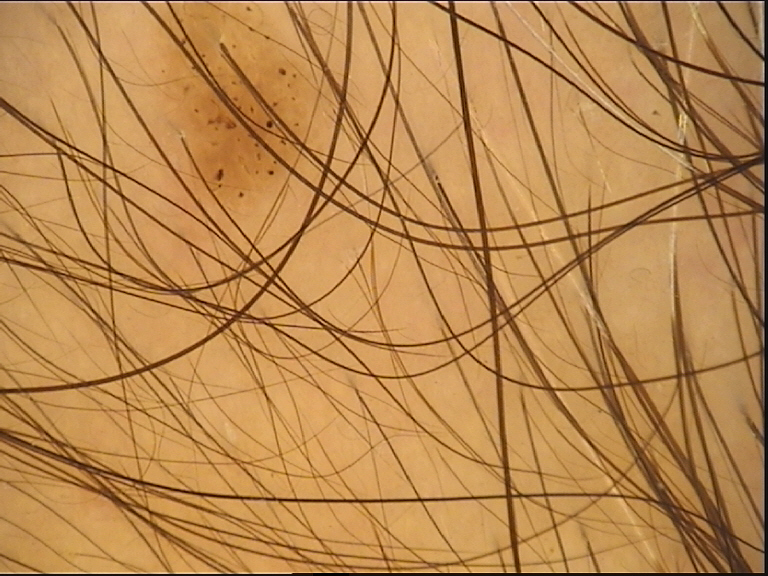Q: What kind of image is this?
A: dermoscopy
Q: What was the diagnostic impression?
A: dysplastic junctional nevus (expert consensus)